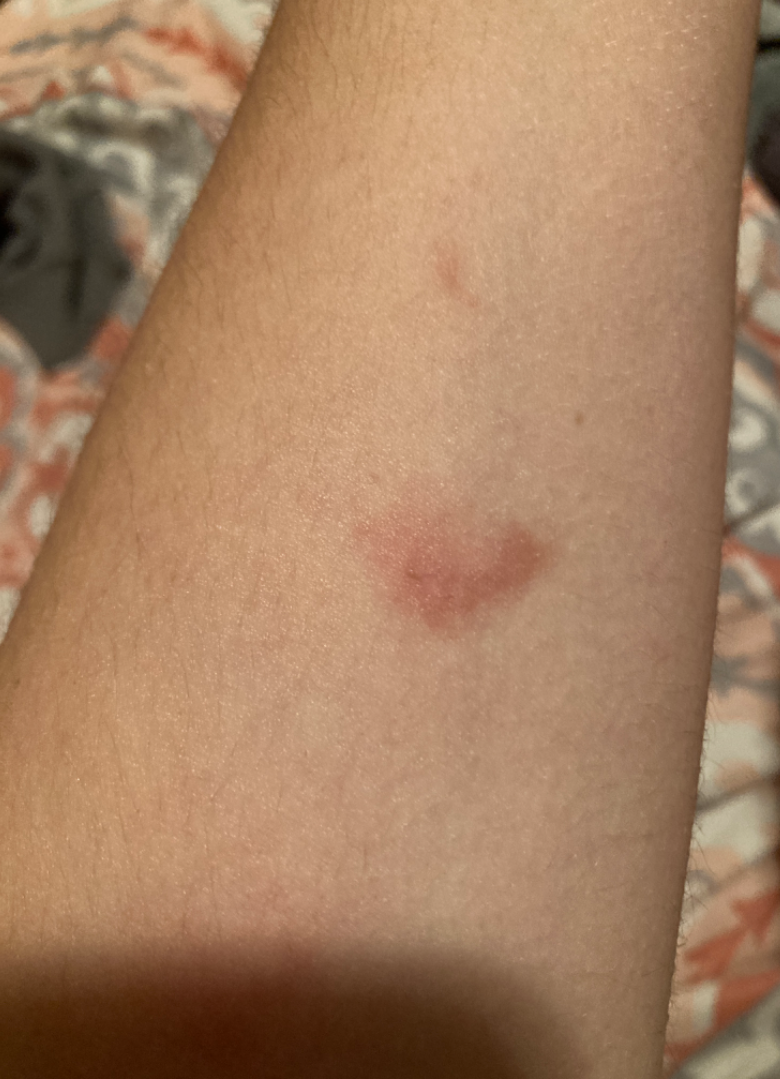image framing — close-up
contributor — female
body site — arm
differential diagnosis — most likely Contact dermatitis; also consider Pigmented purpuric eruption; with consideration of Morphea/Scleroderma; also raised was Post-Inflammatory hyperpigmentation